A skin lesion imaged with a dermatoscope.
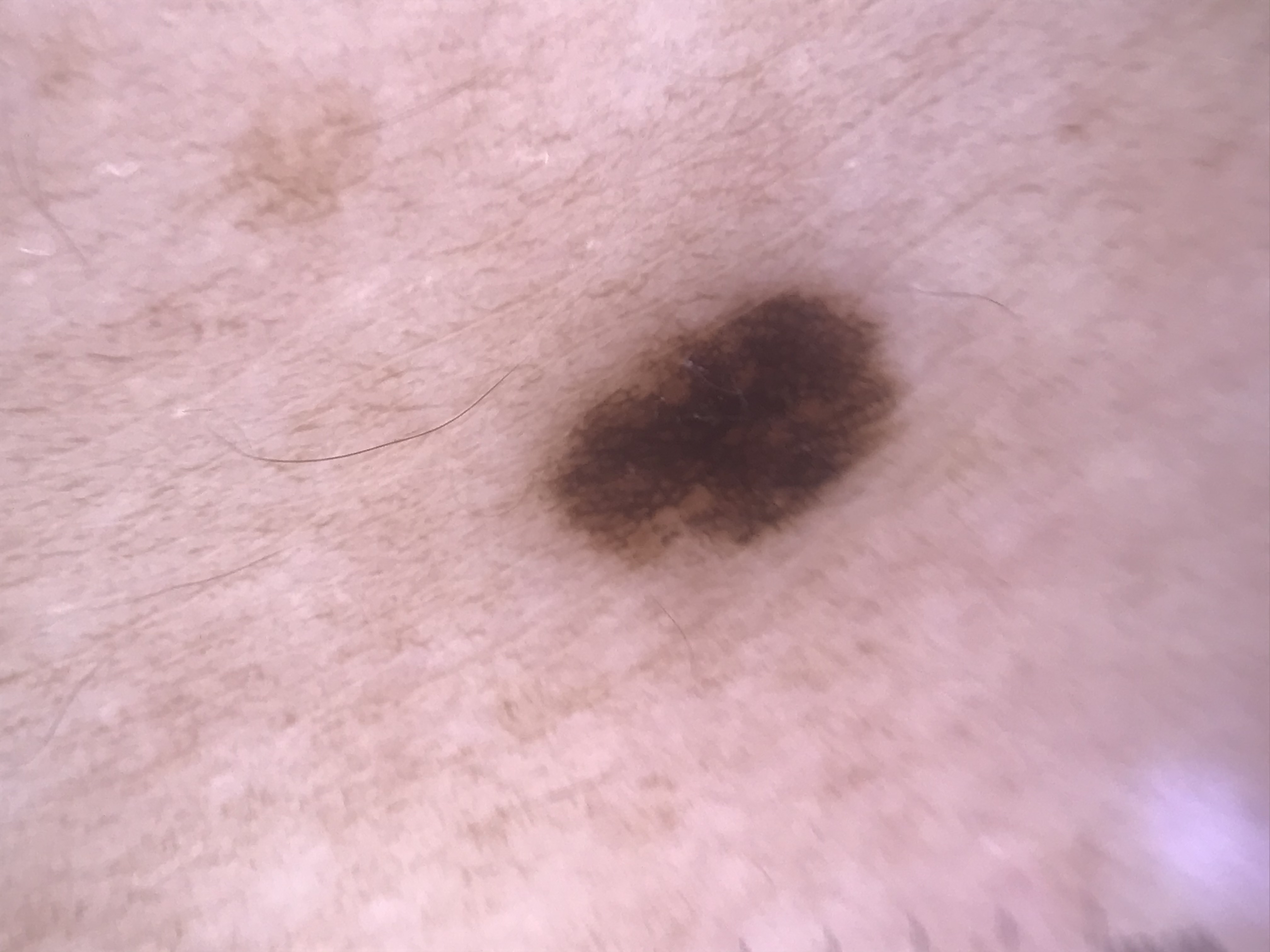Impression:
Classified as a dysplastic junctional nevus.